A male subject 58 years of age.
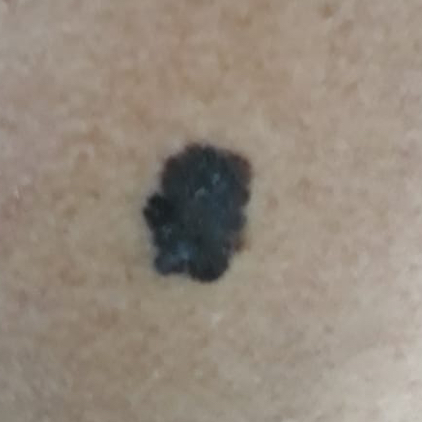site = the back; diagnosis = melanoma (biopsy-proven).